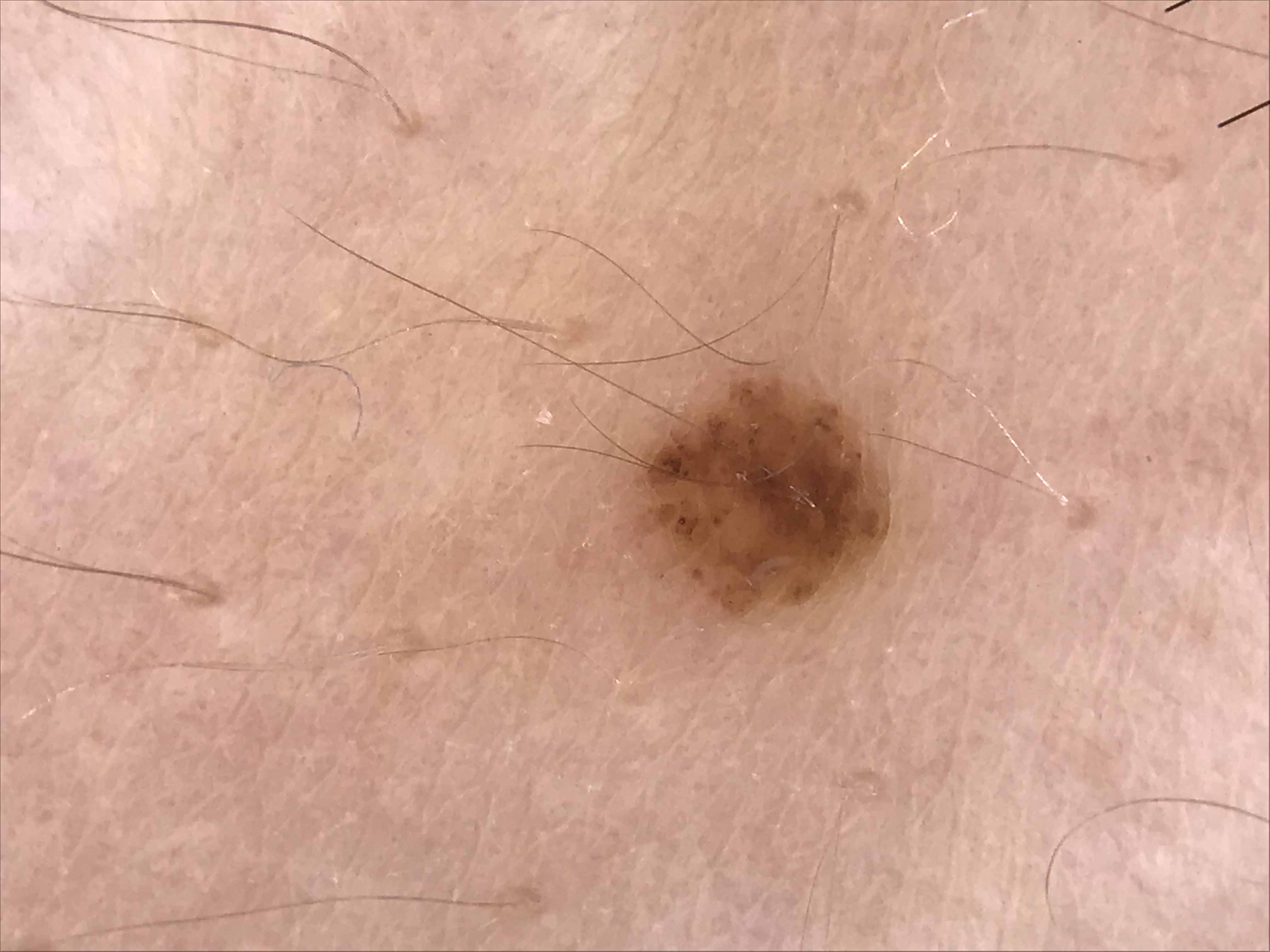Classified as a compound nevus.